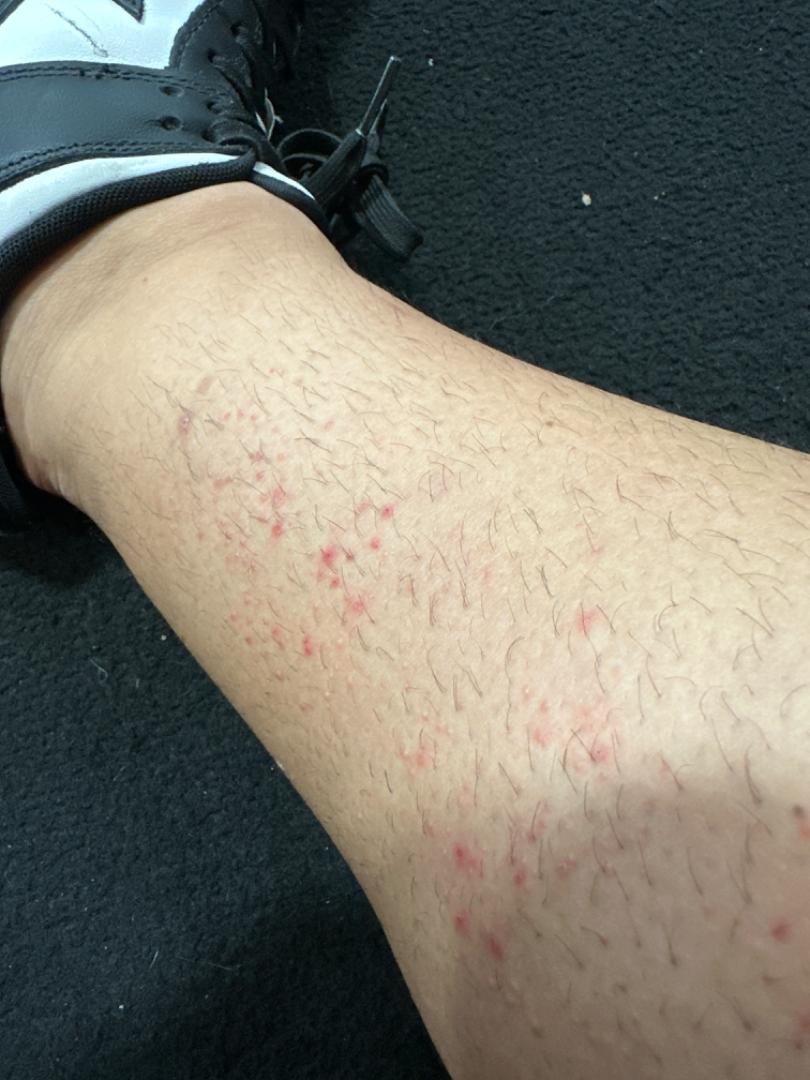Impression:
The skin condition could not be confidently assessed from this image.
History:
The photograph was taken at an angle.